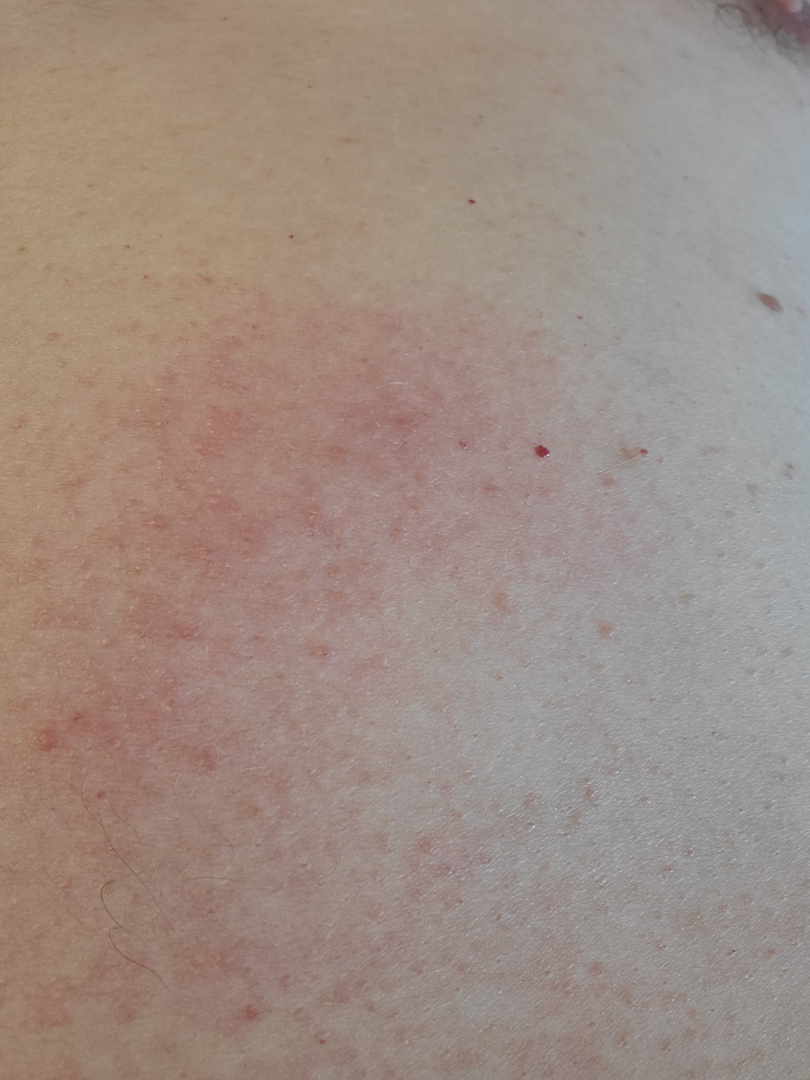Clinical context: The photograph is a close-up of the affected area. The affected area is the front of the torso. Assessment: Single-reviewer assessment: most consistent with Contact dermatitis.